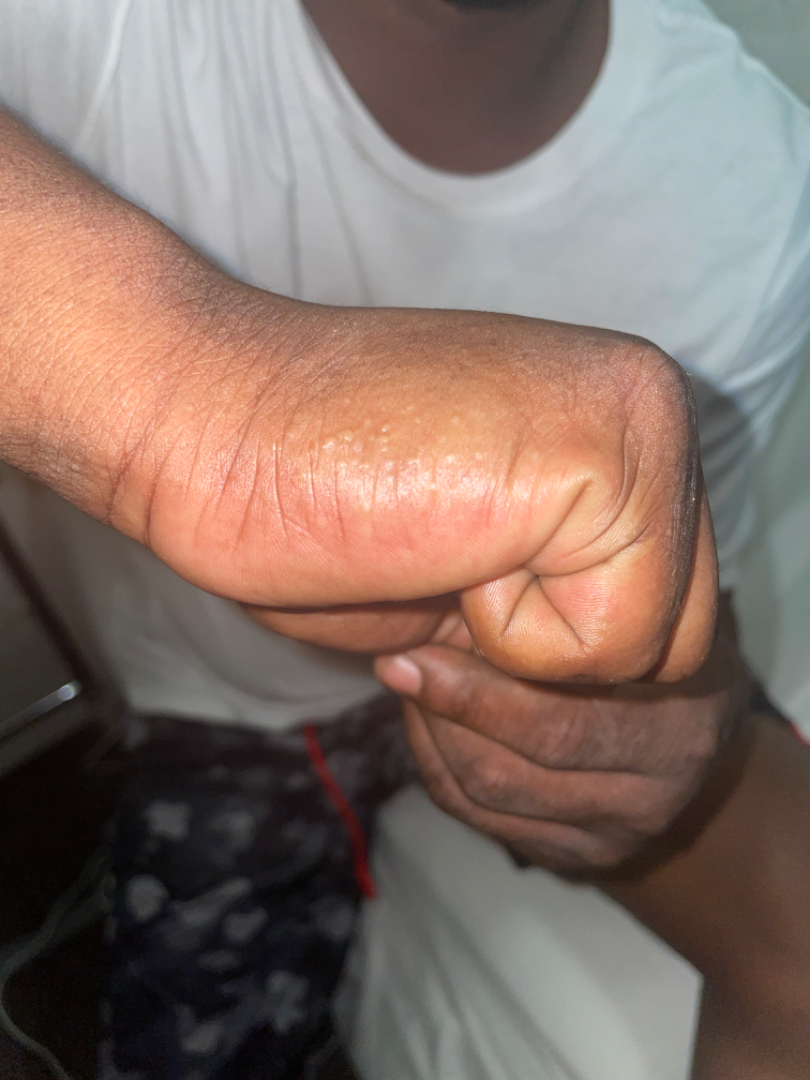Favoring Eczema; also raised was Milia; less likely is Lichen planus/lichenoid eruption.